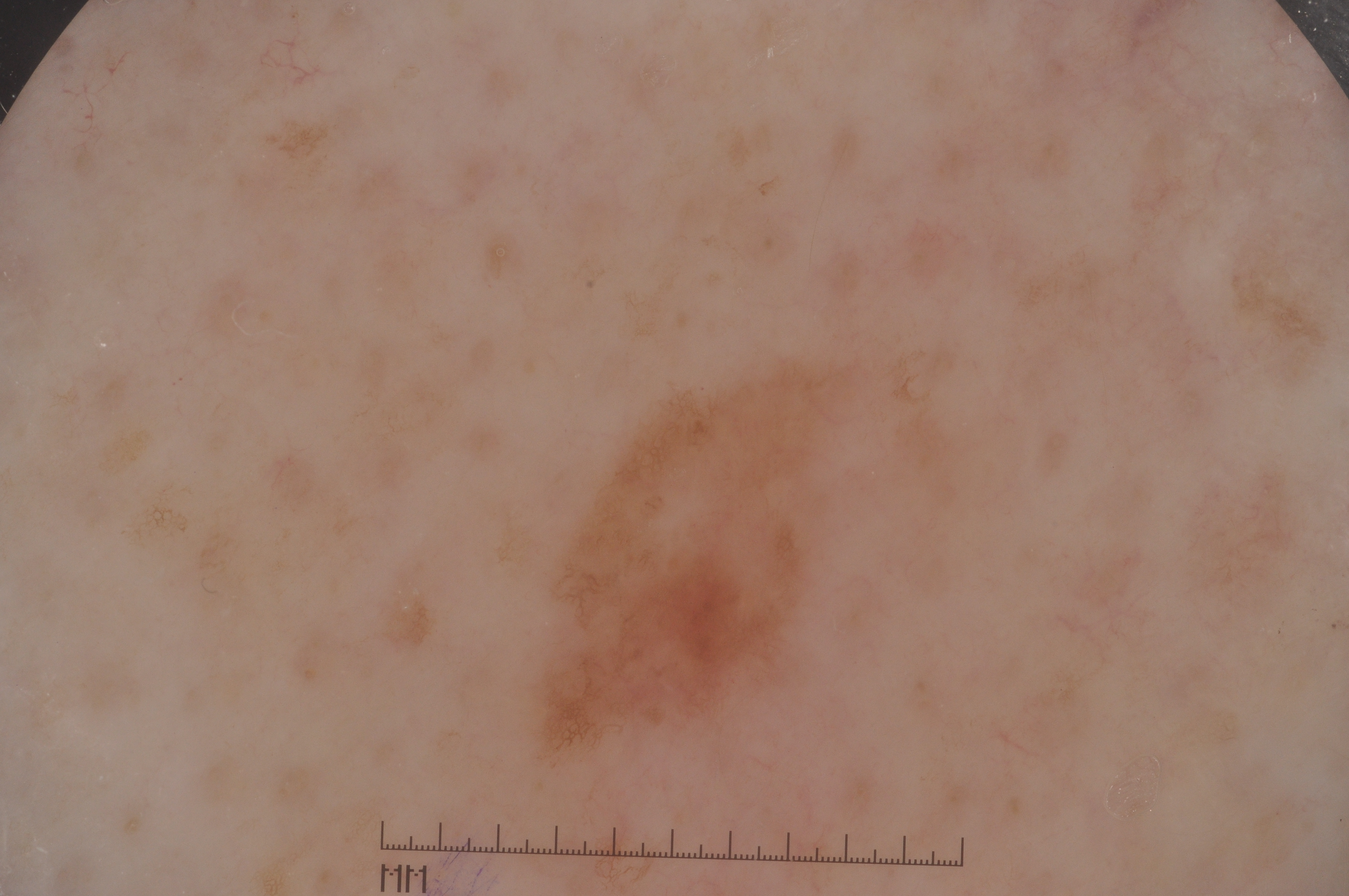Image and clinical context:
The patient is a female about 65 years old. A dermoscopy image of a single skin lesion. As (left, top, right, bottom), the lesion is bounded by 462/306/1015/842. Dermoscopic assessment notes pigment network. The lesion covers approximately 19% of the dermoscopic field.
Conclusion:
Histopathological examination showed a melanoma.